A dermoscopic photograph of a skin lesion.
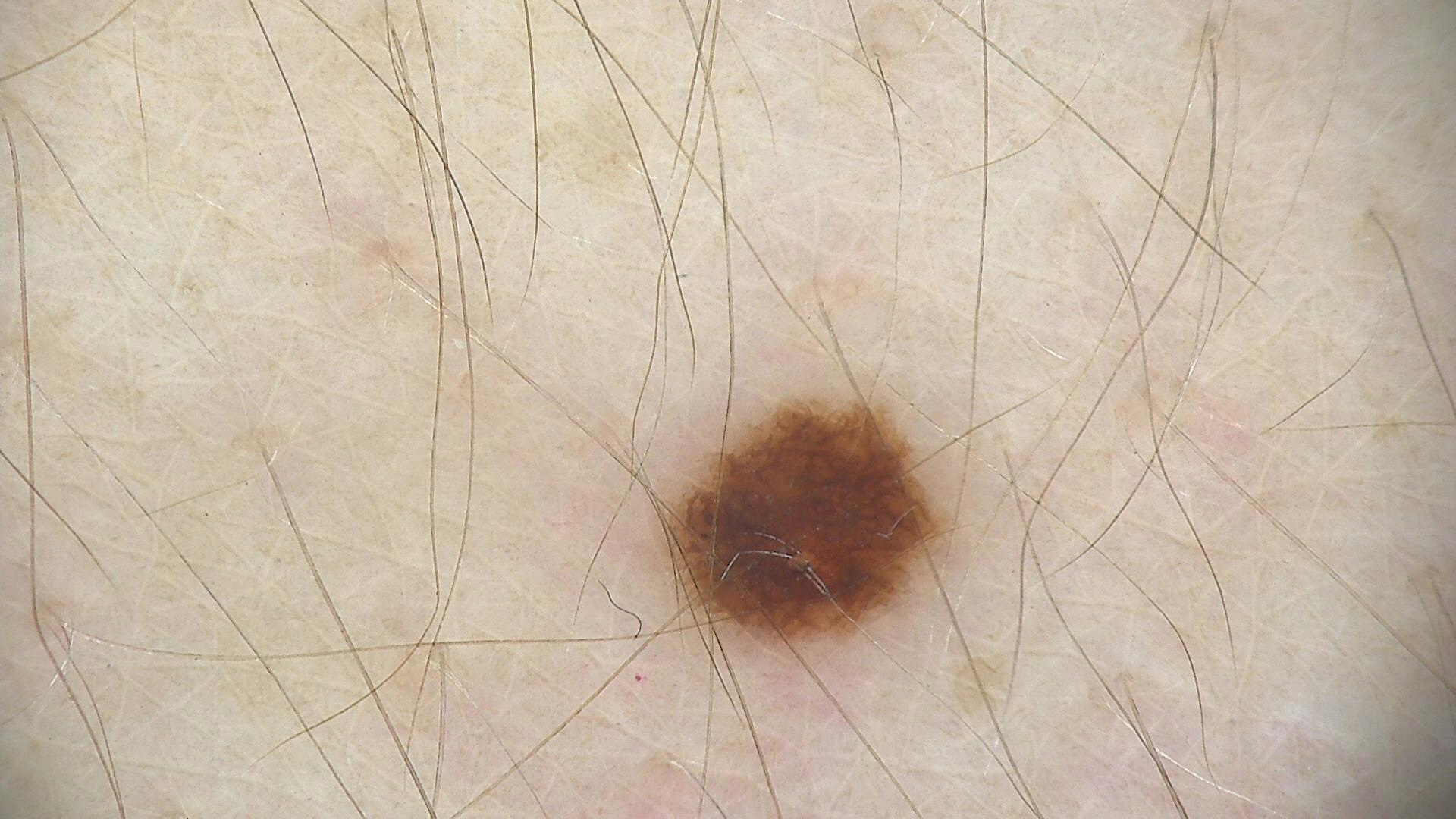Diagnosed as a benign lesion — a dysplastic junctional nevus.